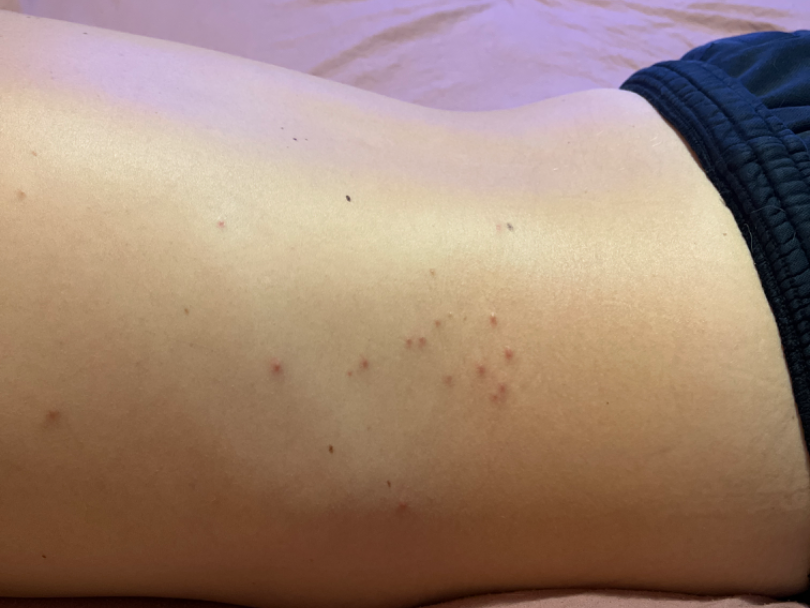assessment = ungradable on photographic review
anatomic site = back of the torso and arm
framing = at a distance